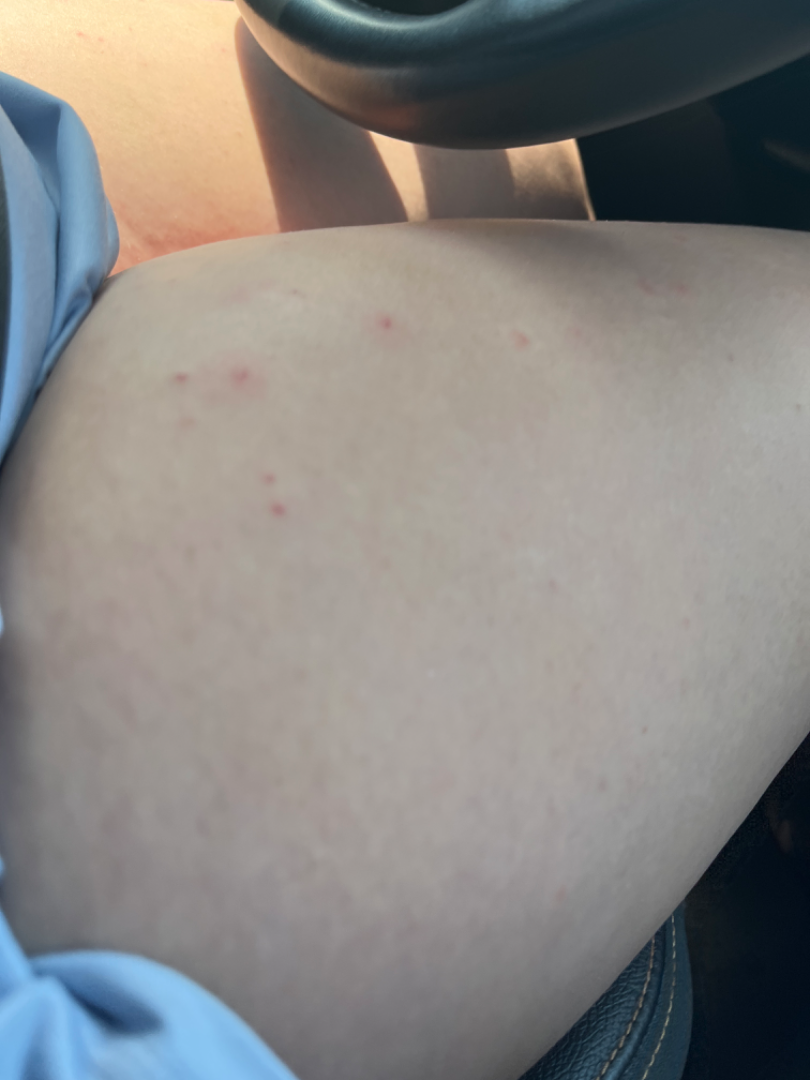affected area — leg
surface texture — raised or bumpy
patient-reported symptoms — bothersome appearance, enlargement and pain
skin tone — Fitzpatrick skin type II
patient — female, age 18–29
shot type — at an angle
symptom duration — about one day
assessment — the favored diagnosis is Folliculitis; with consideration of Keratosis pilaris; an alternative is Irritant Contact Dermatitis